Close-up view. The affected area is the back of the hand: 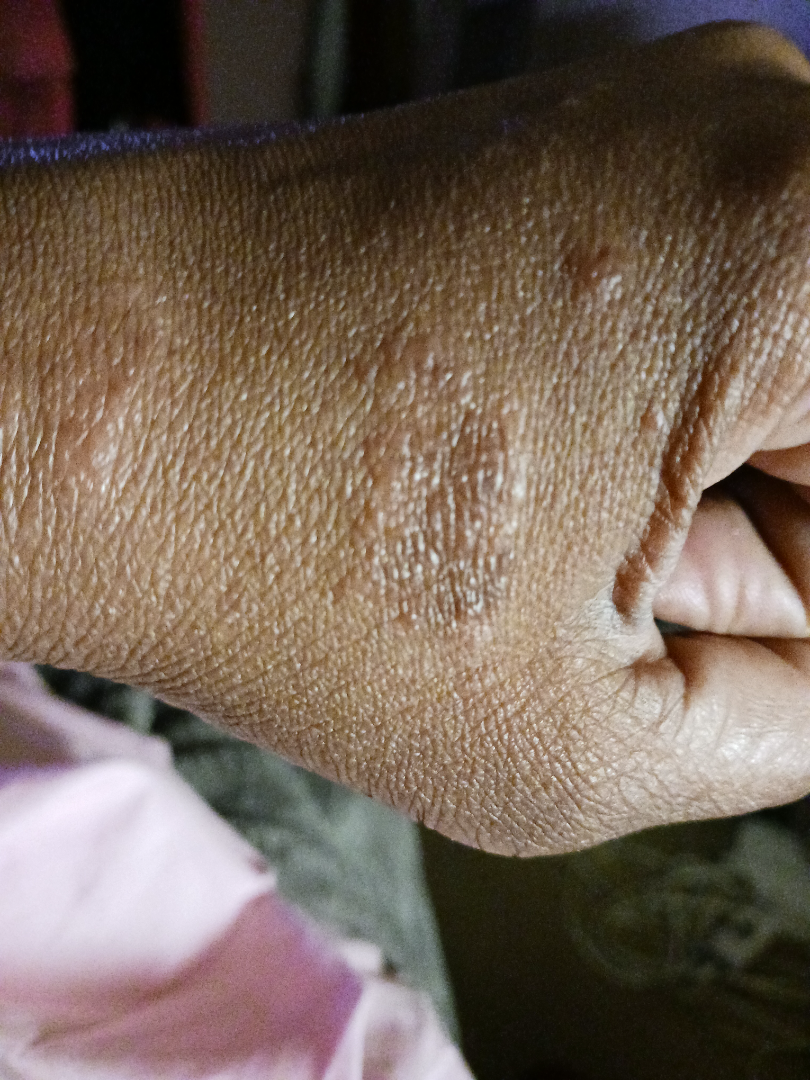differential:
  tied_lead:
    - Cutaneous sarcoidosis
    - Chronic dermatitis, NOS
    - Granuloma annulare